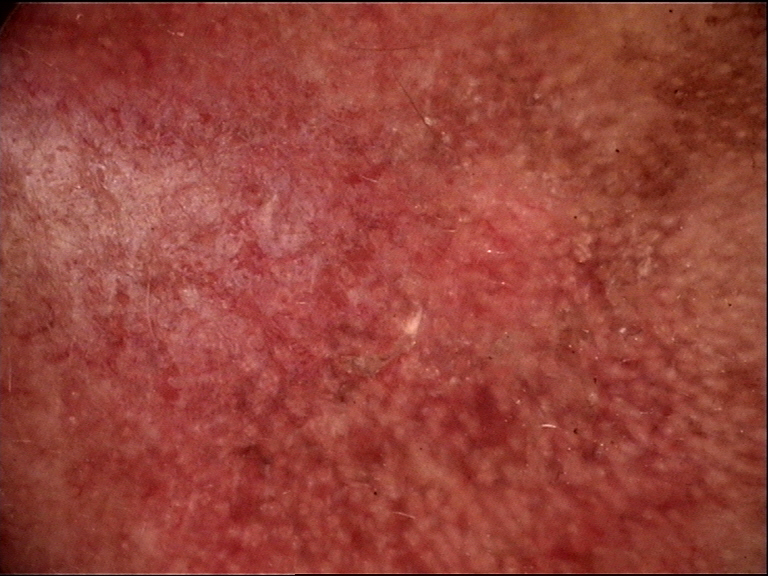diagnosis = actinic keratosis (expert consensus).